A close-up photograph:
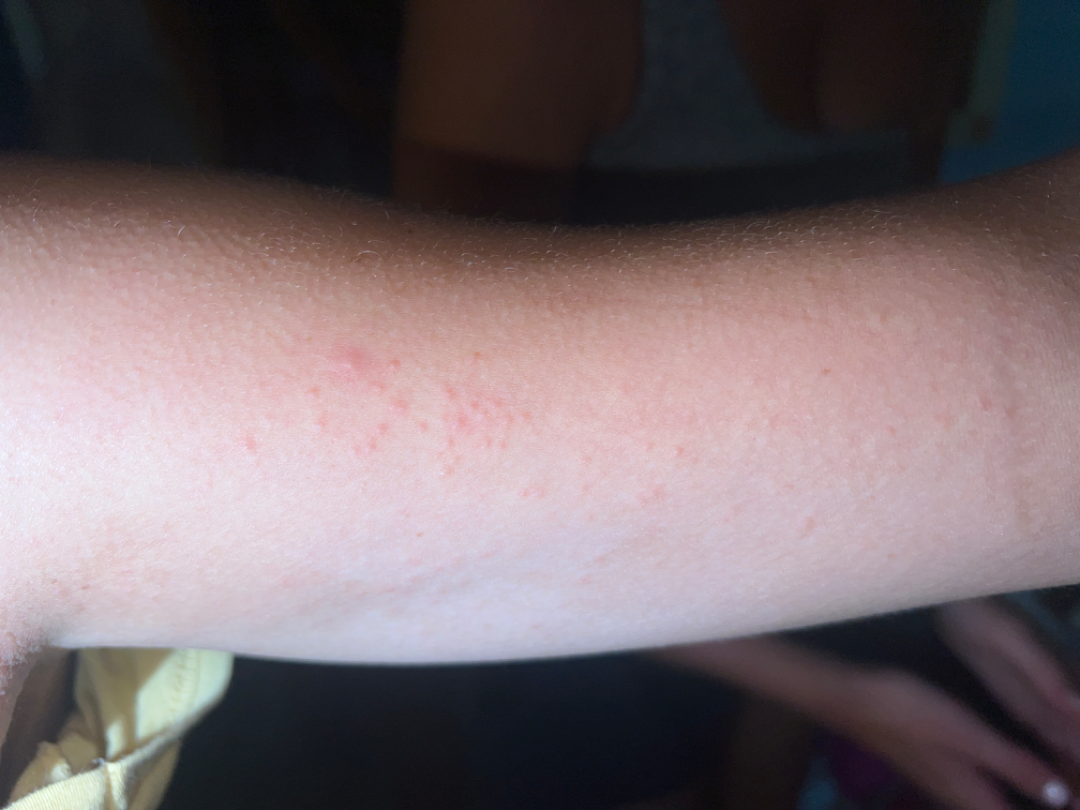Findings:
The reviewer was unable to grade this case for skin condition.